The lesion is associated with pain, bothersome appearance, itching and enlargement · the patient indicates the condition has been present for less than one week · self-categorized by the patient as a rash · the affected area is the leg · the patient indicates associated fever · the photograph is a close-up of the affected area:
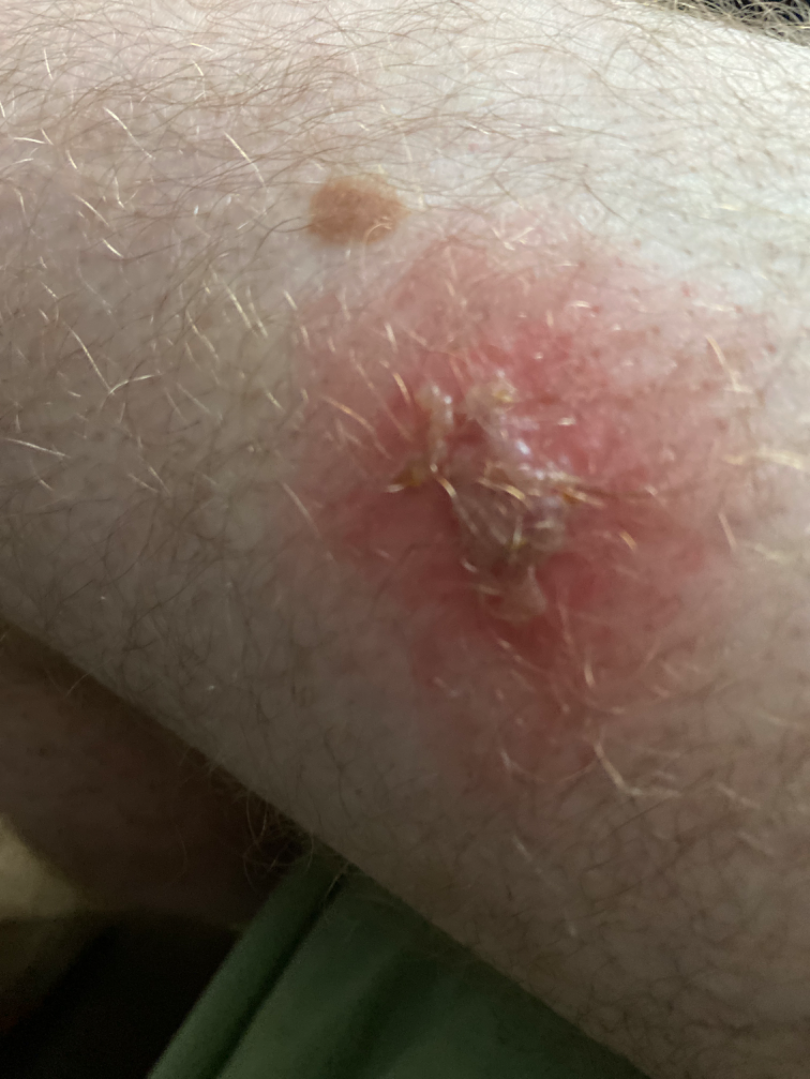The reviewing clinician's impression was: most likely Impetigo; also raised was Secondary impetiginization.